This image was taken at an angle · Fitzpatrick phototype II; lay graders estimated MST 3 or 4 (two reviewer pools) · female subject, age 18–29 · reported lesion symptoms include darkening, bothersome appearance and enlargement · the condition has been present for less than one week · the lesion is described as flat · the lesion involves the leg.
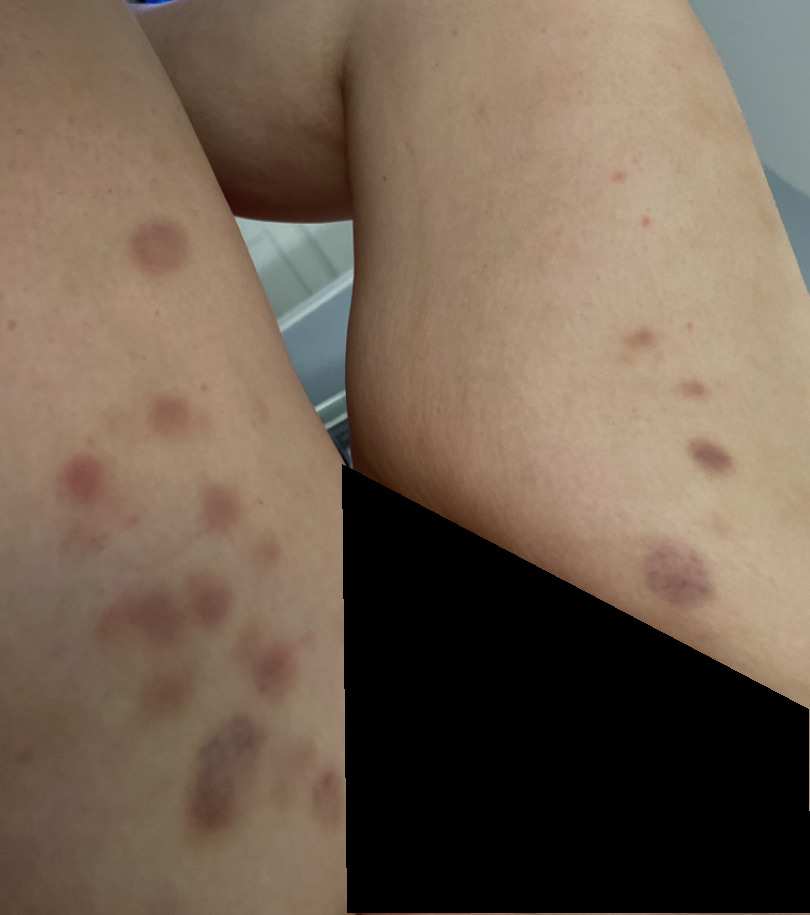{"differential": {"leading": ["ecchymoses"]}}